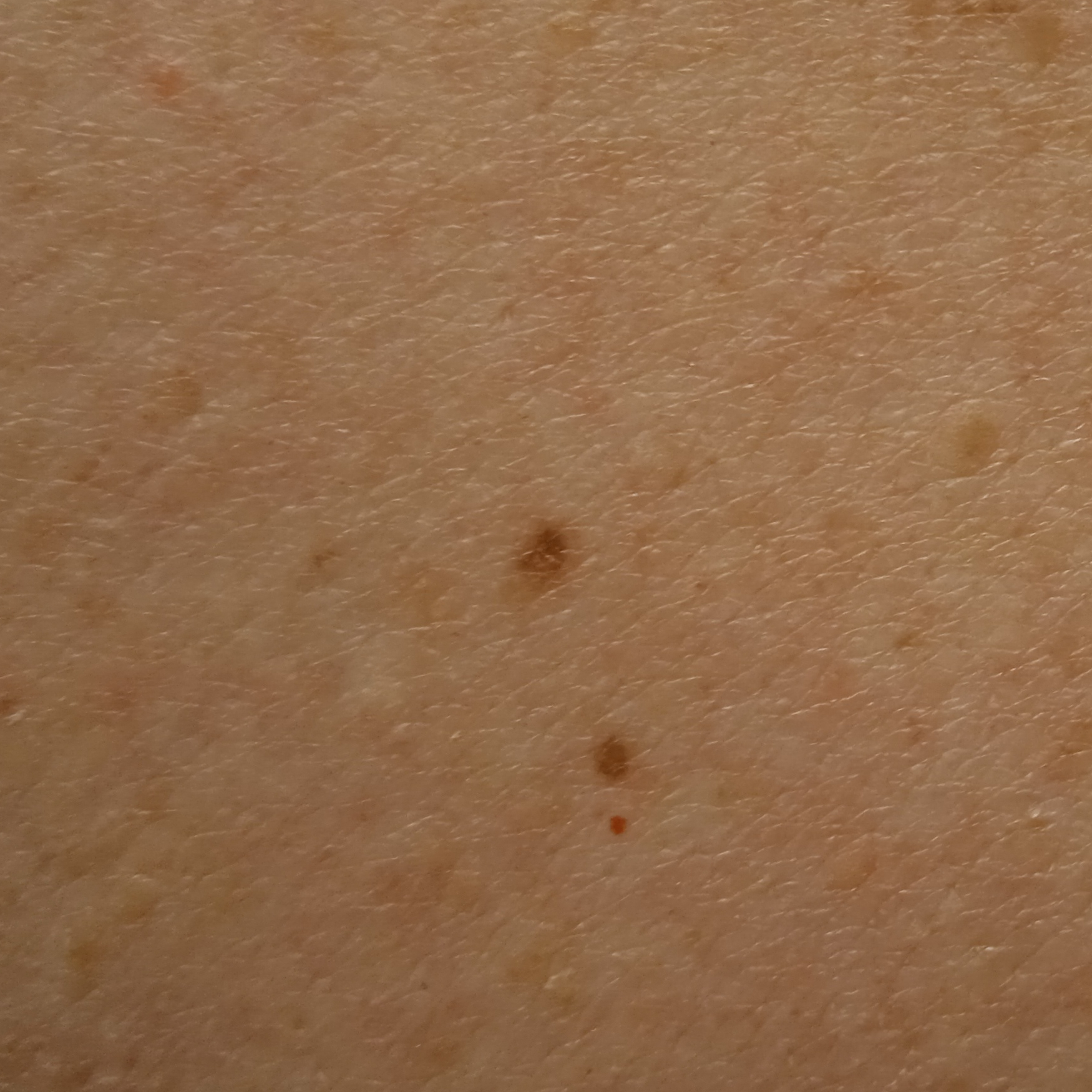| feature | finding |
|---|---|
| referral | research study (no referral diagnosis) |
| risk factors | immunosuppression, a prior organ transplant |
| nevus count | a moderate number of melanocytic nevi |
| sun reaction | skin reddens painfully with sun exposure |
| anatomic site | the back |
| lesion size | 2.5 mm |
| diagnosis | melanocytic nevus (dermatologist consensus) |